Few moles overall by the patient's own estimate · acquired for a research image collection, with no referral diagnosis: 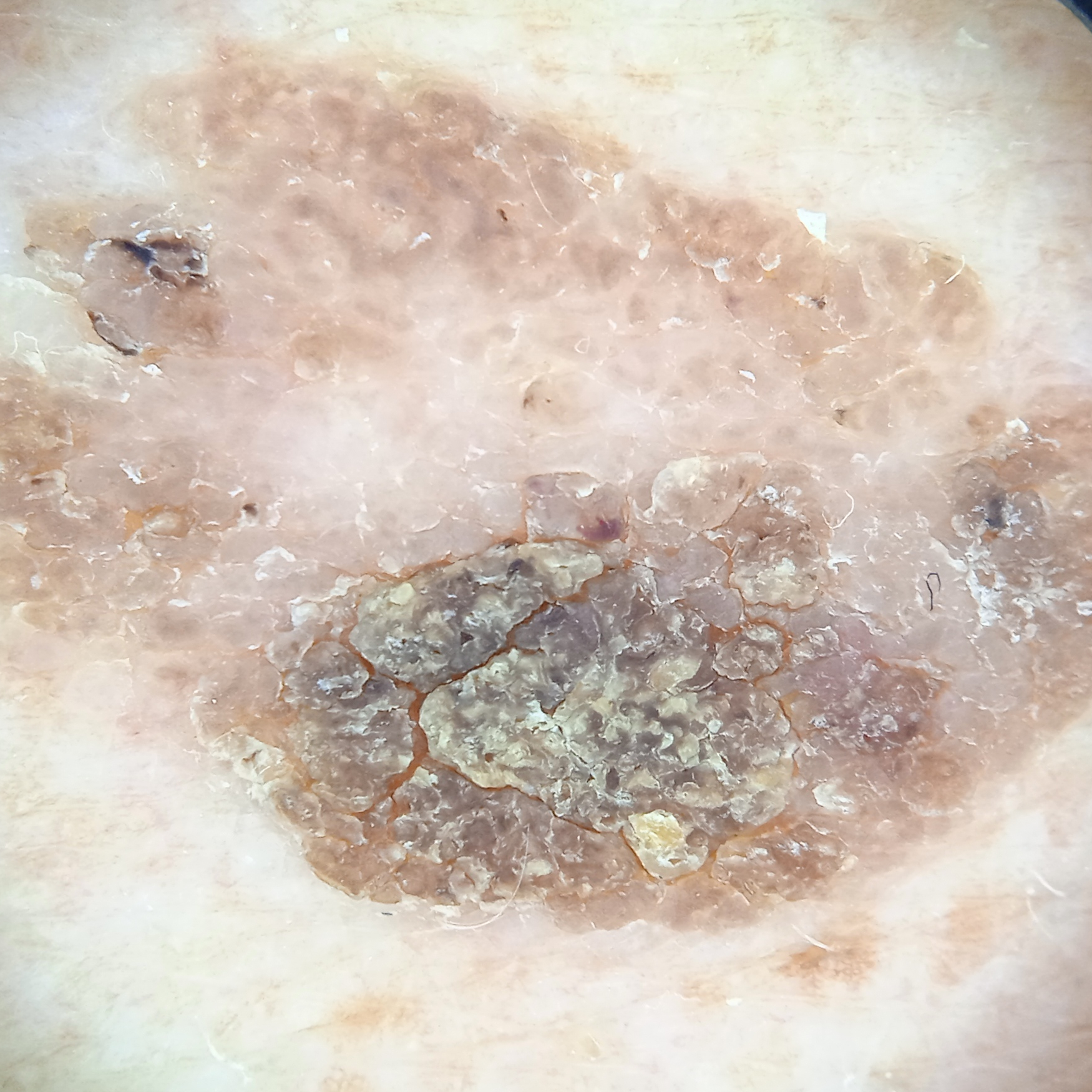Located on the back. The consensus diagnosis for this lesion was a seborrheic keratosis.